A skin lesion imaged with a dermatoscope:
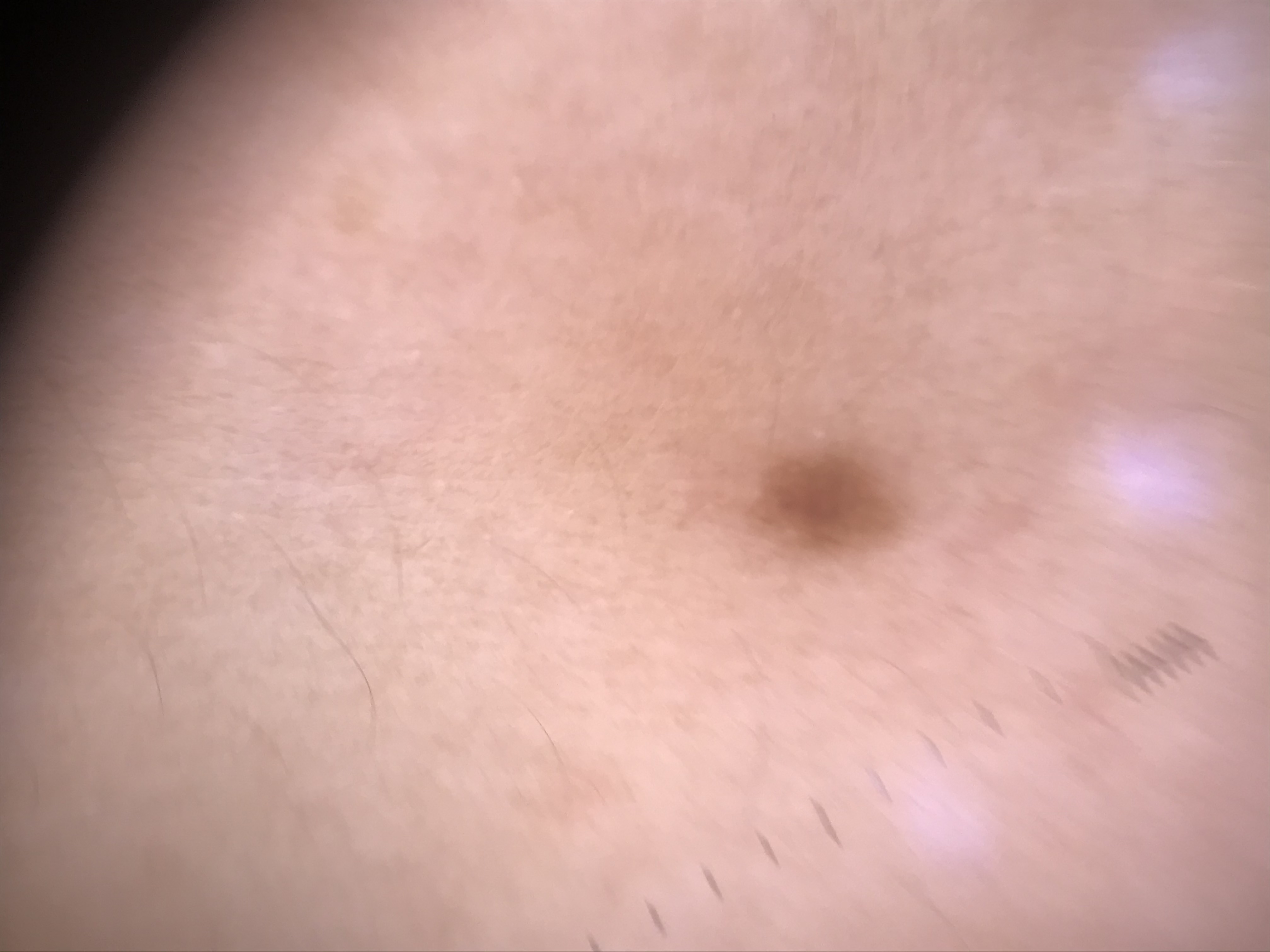lesion type = banal | class = junctional nevus (expert consensus).